A skin lesion imaged with a dermatoscope.
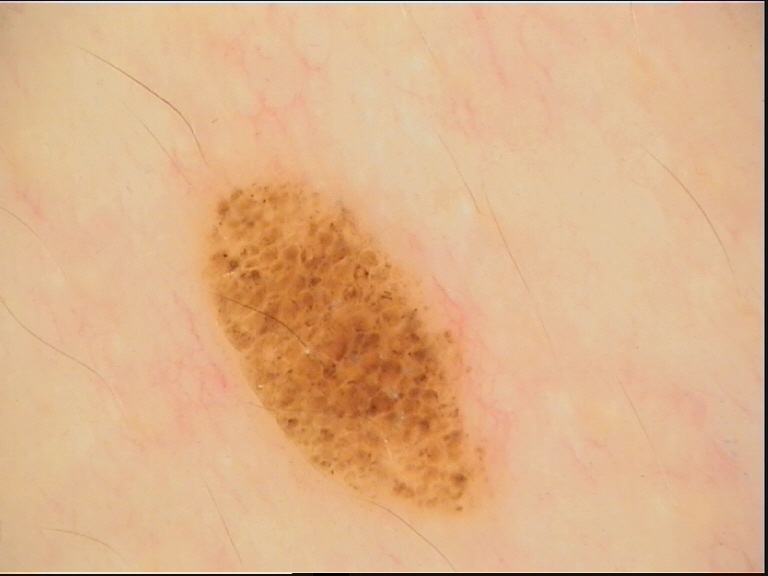Impression: Classified as a benign lesion — a dysplastic compound nevus.